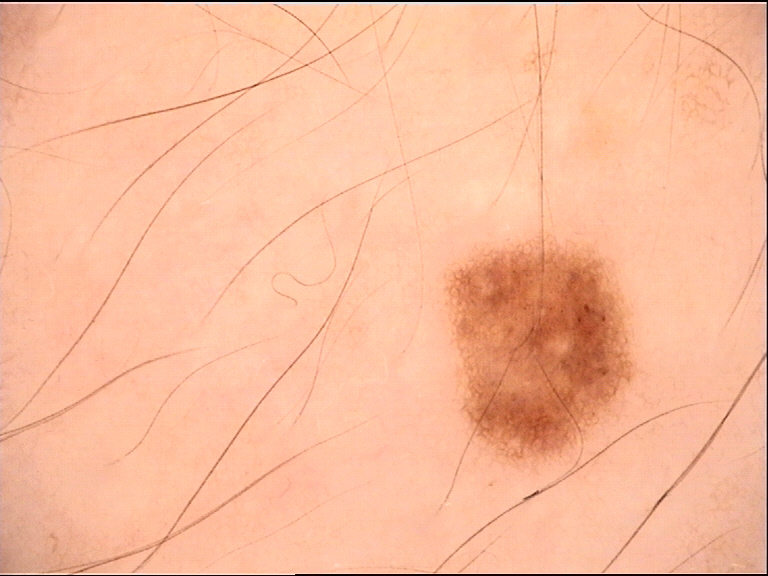modality: dermoscopy
label: dysplastic junctional nevus (expert consensus)